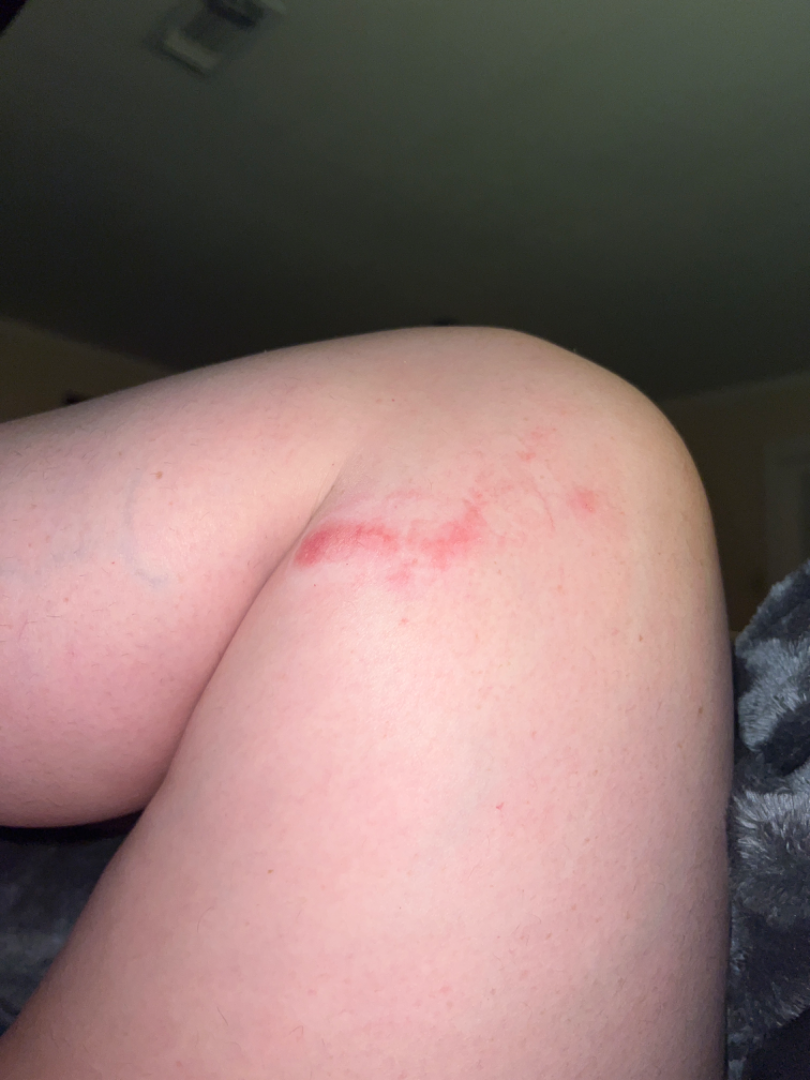The photo was captured at a distance.
The affected area is the leg.
On teledermatology review, Allergic Contact Dermatitis (1.00).